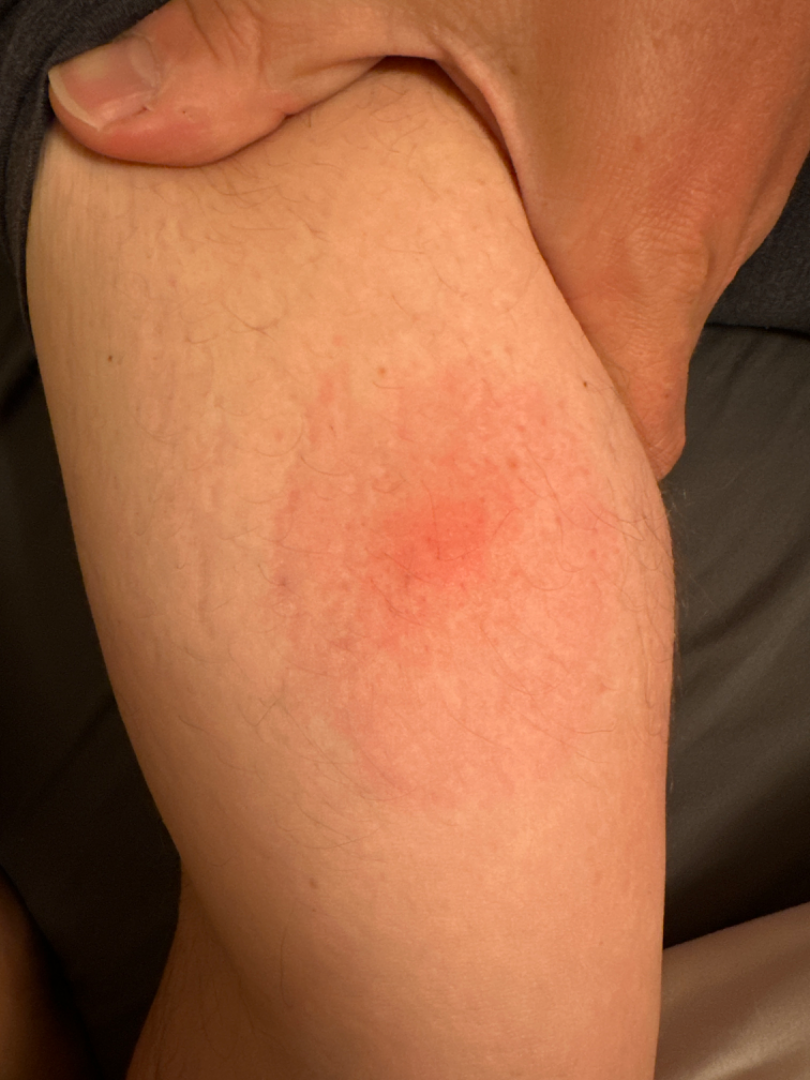anatomic site: arm | view: close-up | texture: raised or bumpy | history: less than one week | patient-reported symptoms: itching and enlargement | impression: favoring Erythema migrans; possibly Cellulitis; an alternative is Insect Bite.